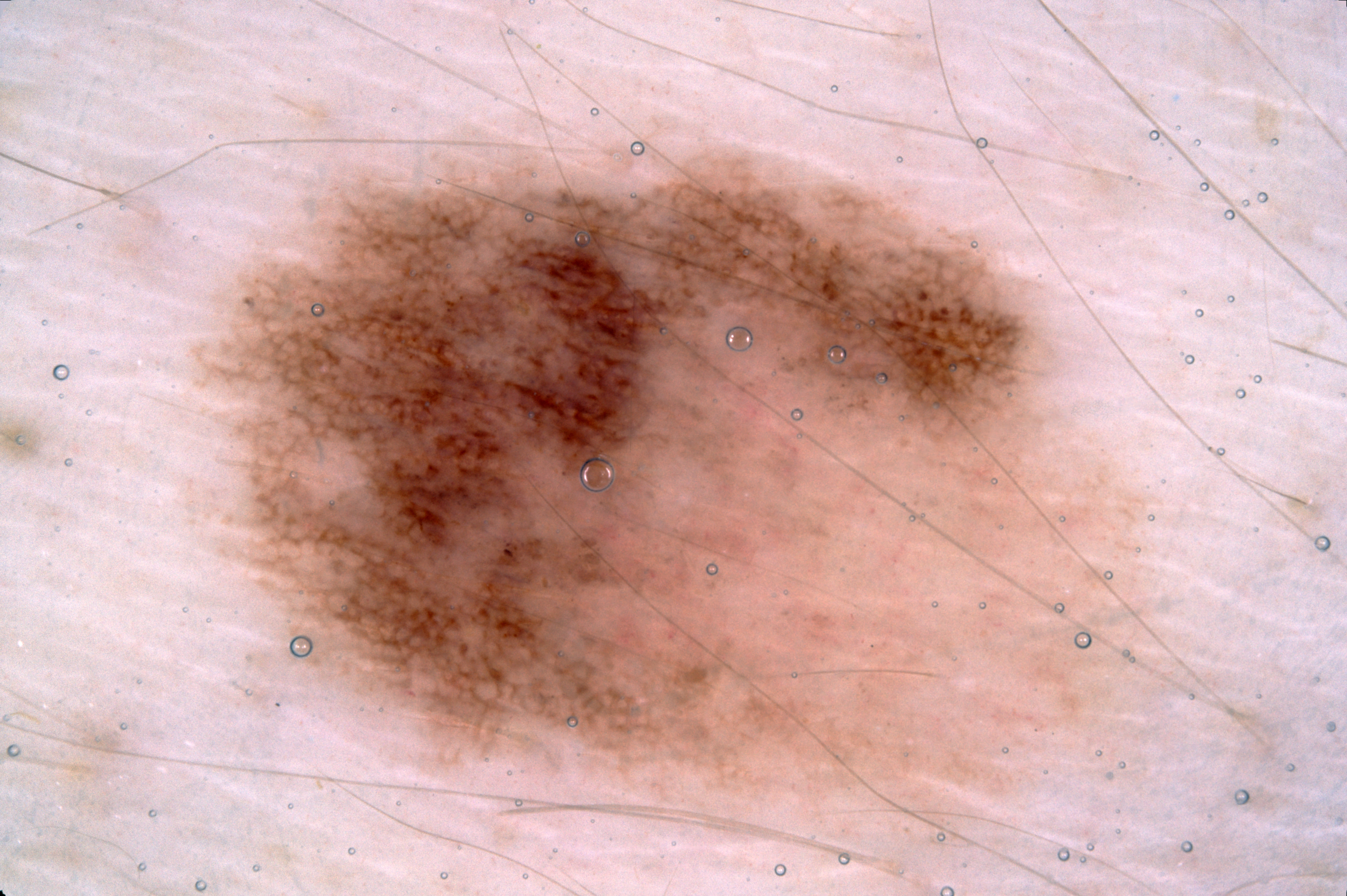Dermoscopy of a skin lesion.
A male patient, aged 18 to 22.
The visible lesion spans <bbox>191, 133, 1165, 849</bbox>.
Dermoscopic assessment notes pigment network.
Consistent with a melanocytic nevus, a benign skin lesion.